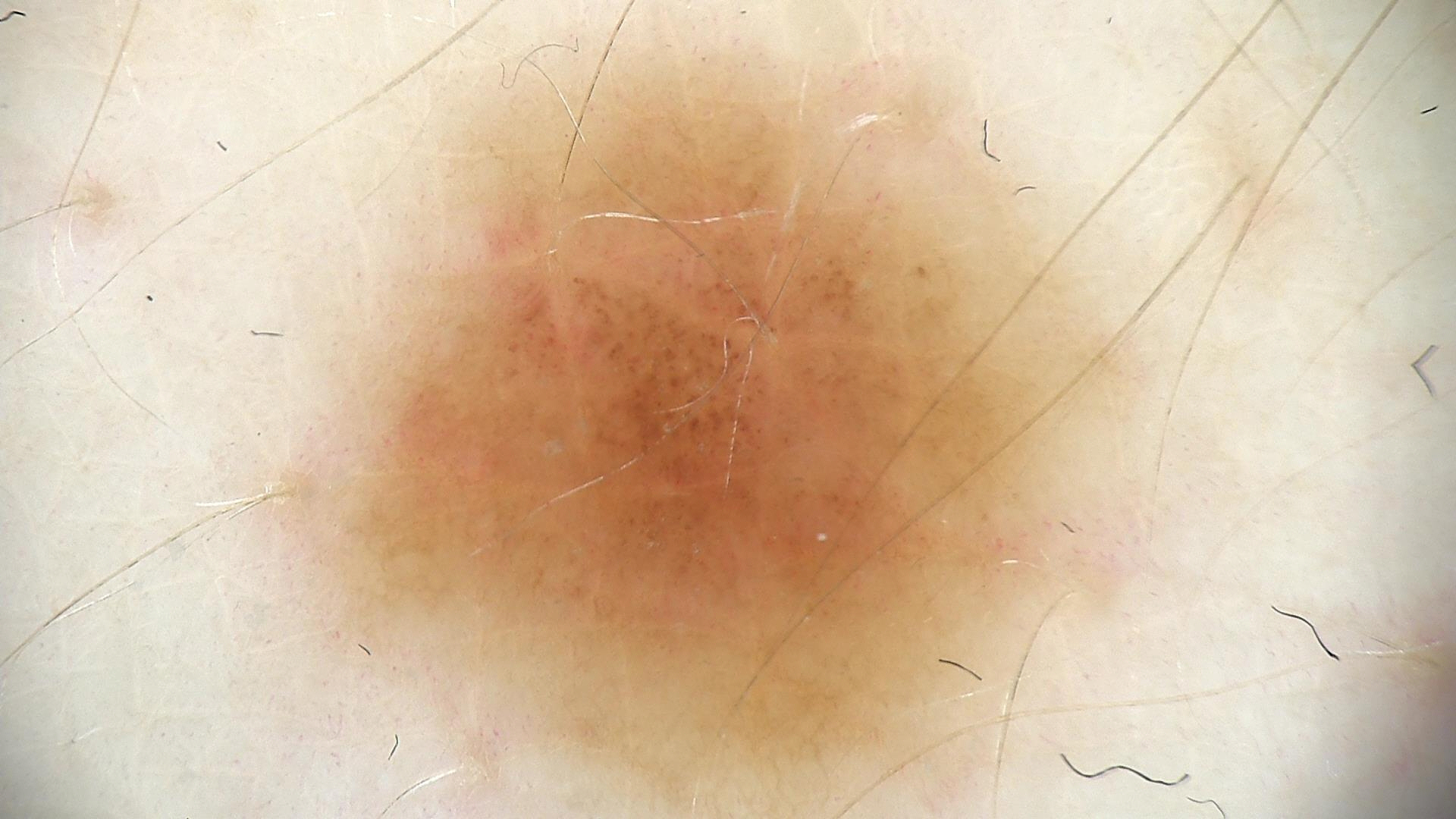The diagnosis was a benign lesion — a dysplastic junctional nevus.